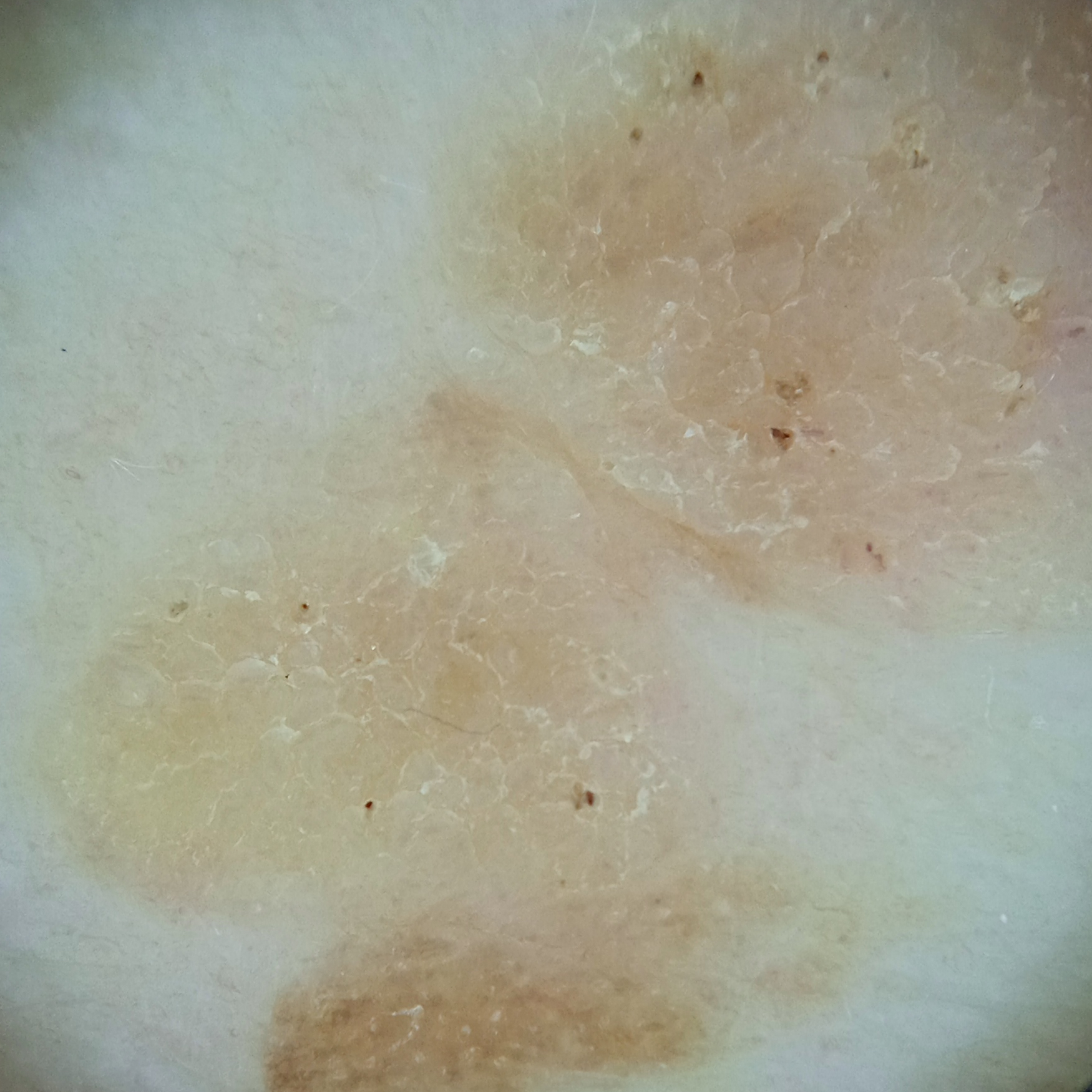assessment = seborrheic keratosis (dermatologist consensus).